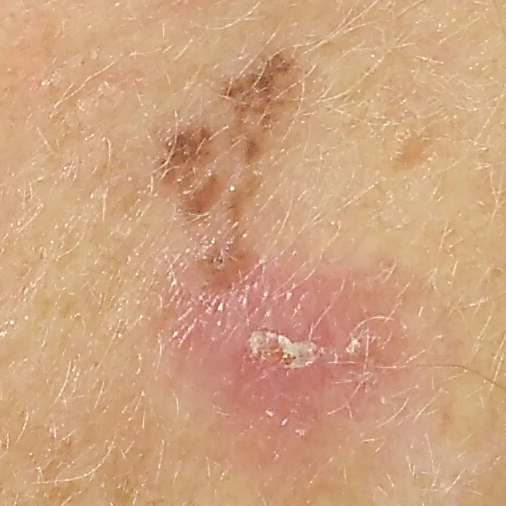Q: How was this image acquired?
A: clinical photo
Q: Skin phototype?
A: II
Q: What are the relevant risk factors?
A: pesticide exposure, prior skin cancer (patient or family), no prior malignancy (patient or family), no alcohol use
Q: Tell me about the patient.
A: female, in their mid-60s
Q: Where on the body is the lesion?
A: the face
Q: How large is the lesion?
A: 16x15 mm
Q: What does the patient describe?
A: growth / no pain, no elevation
Q: What is this lesion?
A: basal cell carcinoma (biopsy-proven)